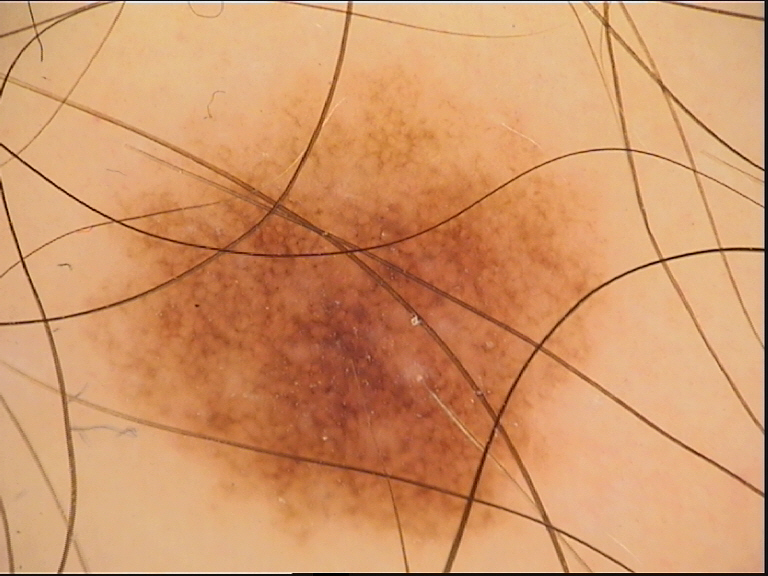image type: dermatoscopy; diagnostic label: dysplastic junctional nevus (expert consensus).